A male subject, aged 53-57 · a dermoscopic image of a skin lesion — 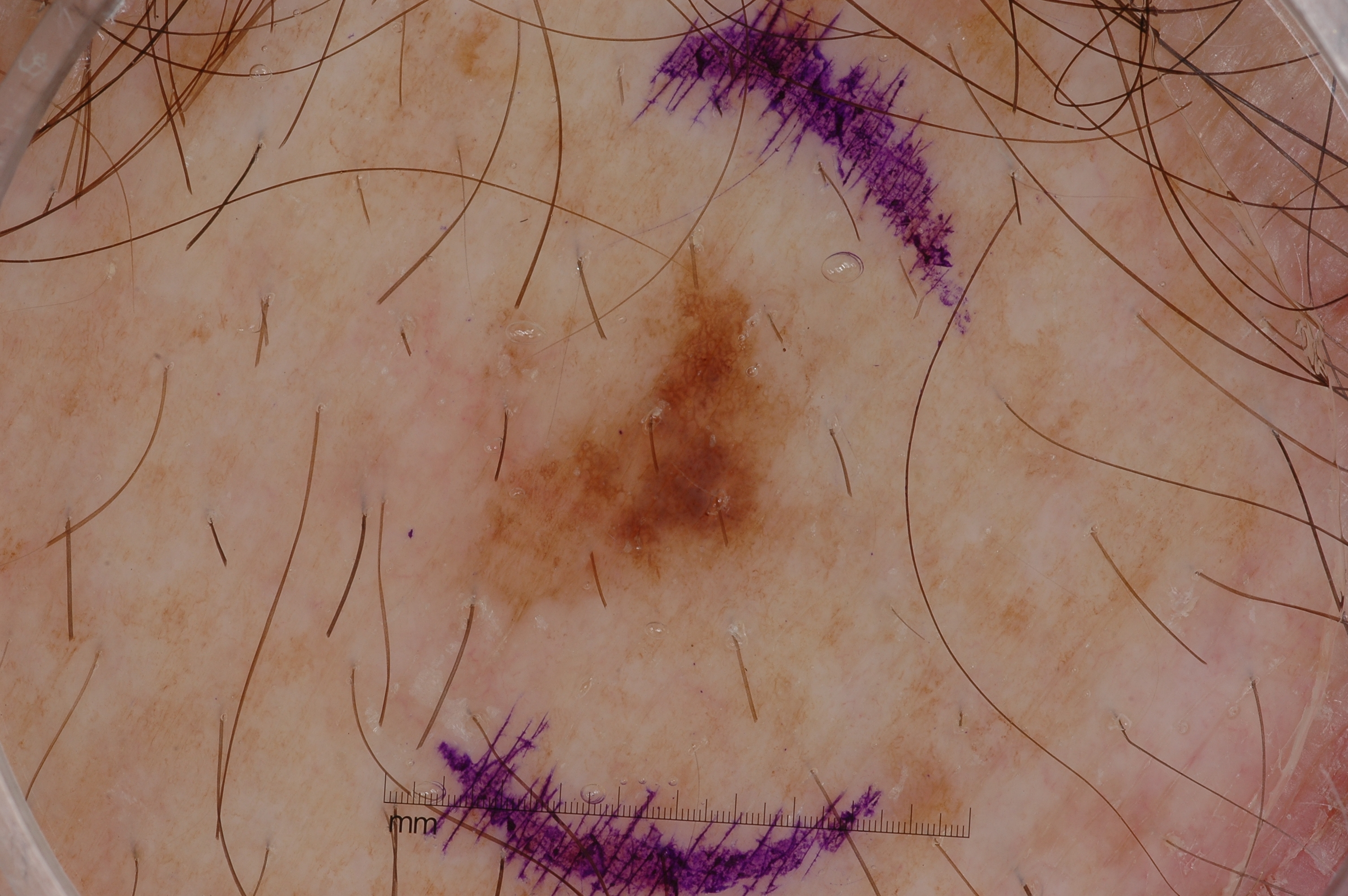Findings:
As (left, top, right, bottom), the lesion's extent is <box>462, 228, 825, 663</box>. The dermoscopic pattern shows pigment network; no milia-like cysts, streaks, or negative network.
Impression:
Expert review diagnosed this as a melanocytic nevus.